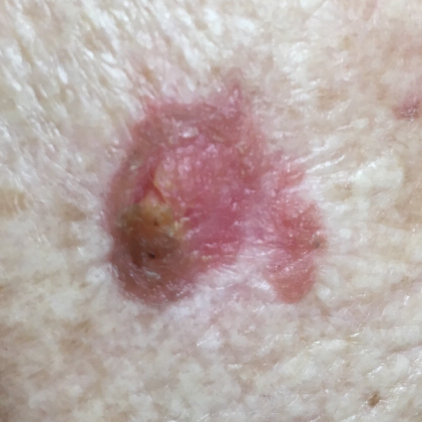Histopathology confirmed a squamous cell carcinoma.